Female patient, age 30–39; this is a close-up image — 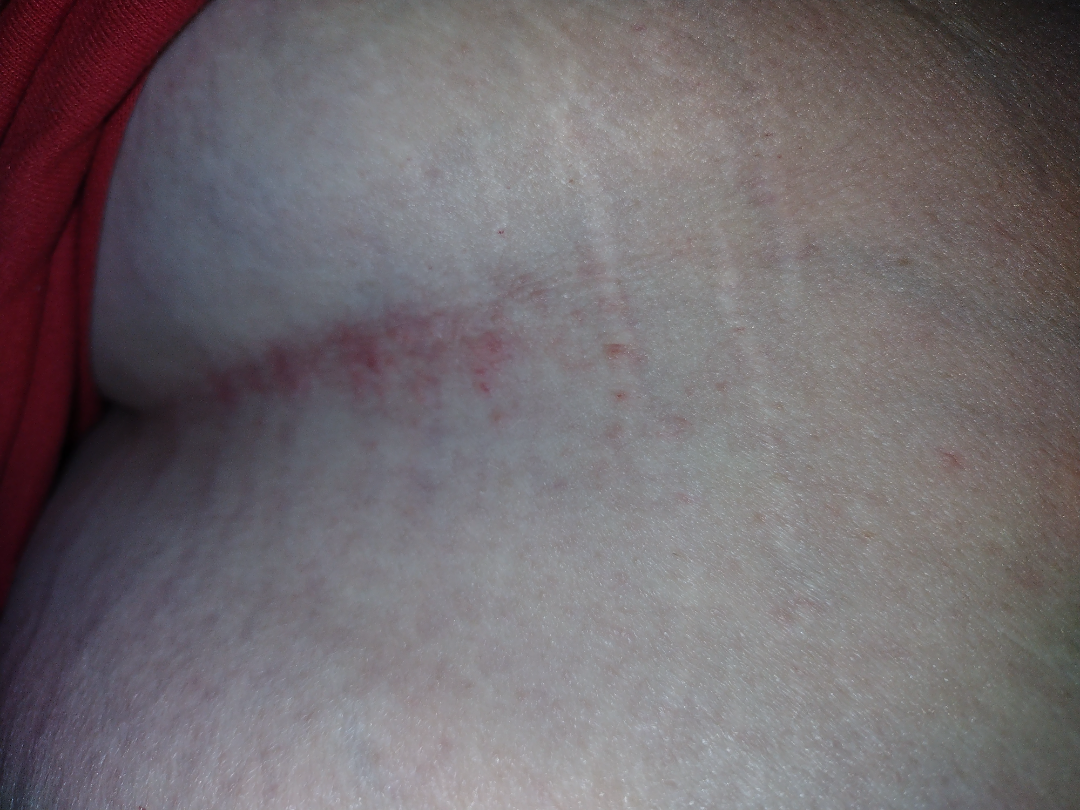Patient information: The patient reports the lesion is raised or bumpy. Self-categorized by the patient as a rash. Fitzpatrick phototype V. The patient reports enlargement and itching. The patient reports the condition has been present for one to four weeks. Review: Consistent with Irritant Contact Dermatitis.